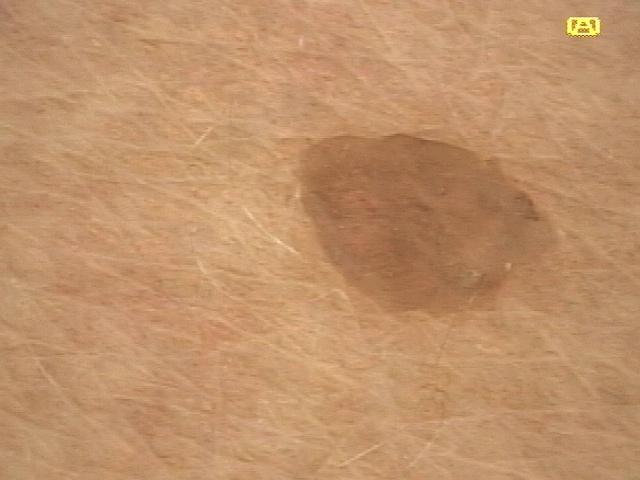A female patient aged 53-57. Recorded as Fitzpatrick skin type II. A dermoscopic close-up of a skin lesion. The lesion was found on the posterior trunk. Consistent with a nevus.